The subject is 40–49, male; the affected area is the back of the torso, front of the torso and arm; this image was taken at an angle.
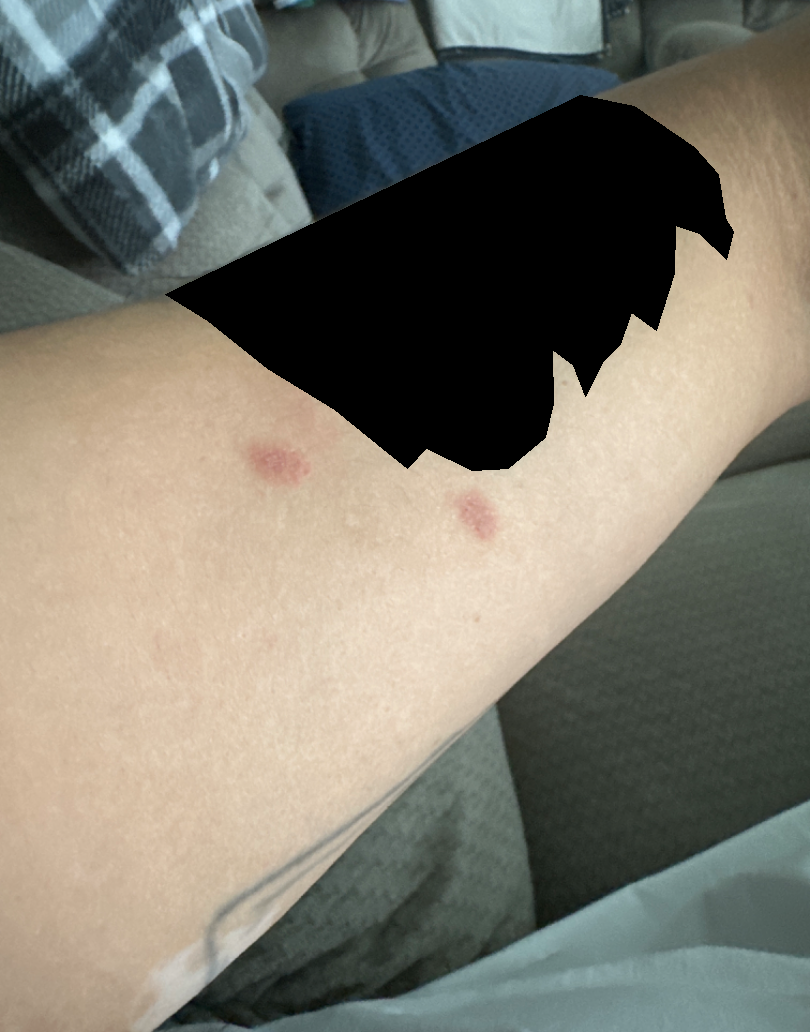{"differential": {"leading": ["Acute constitutional eczema"], "considered": ["Infestation caused by Sarcoptes scabiei var bovis"]}}